Fitzpatrick skin type II; non-clinician graders estimated MST 2 or 3 · the back of the hand and arm are involved · the patient notes bothersome appearance and bleeding · the subject is a female aged 60–69 · this is a close-up image · the patient considered this a rash · texture is reported as fluid-filled · present for more than five years — 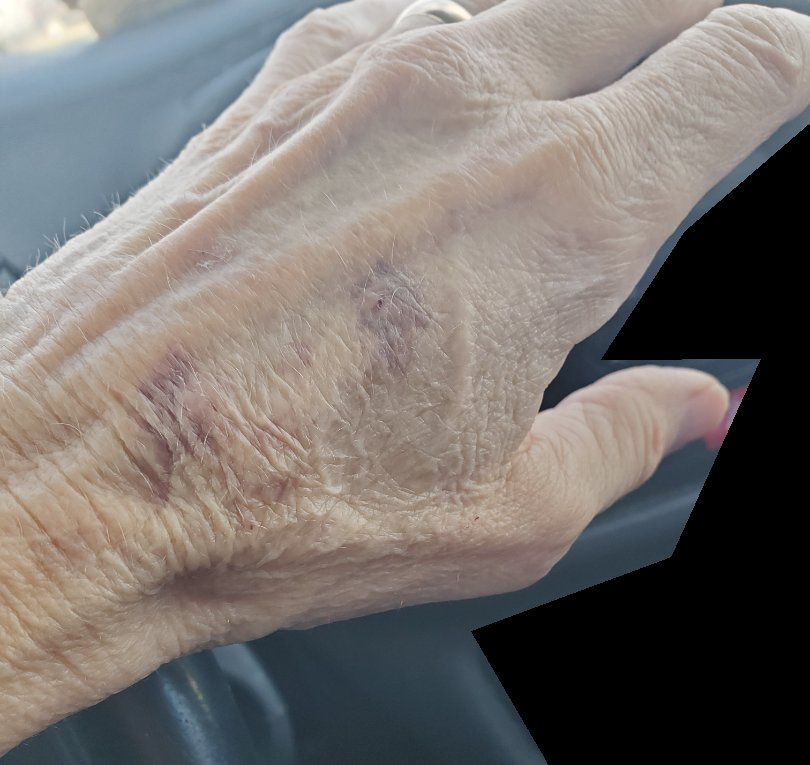{
  "differential": {
    "leading": [
      "ecchymoses"
    ]
  }
}